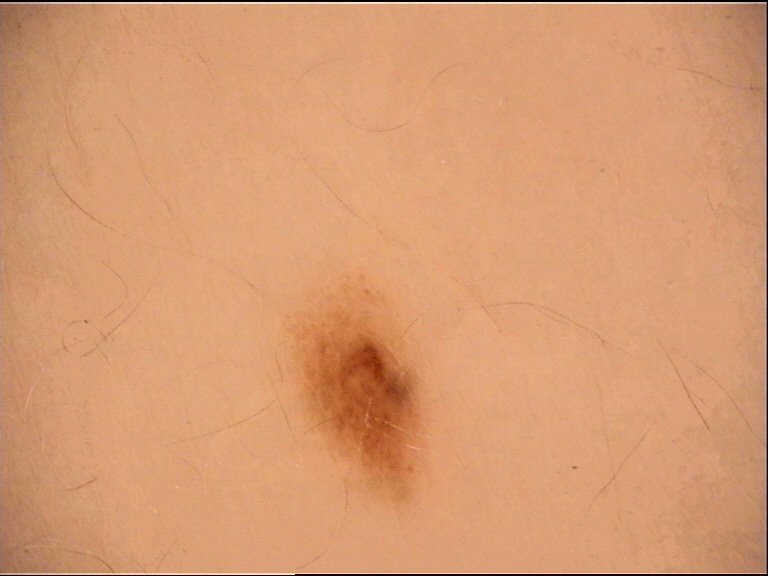Findings: A dermoscopy image of a single skin lesion. Impression: Consistent with a benign lesion — a dysplastic junctional nevus.